Dermoscopy of a skin lesion:
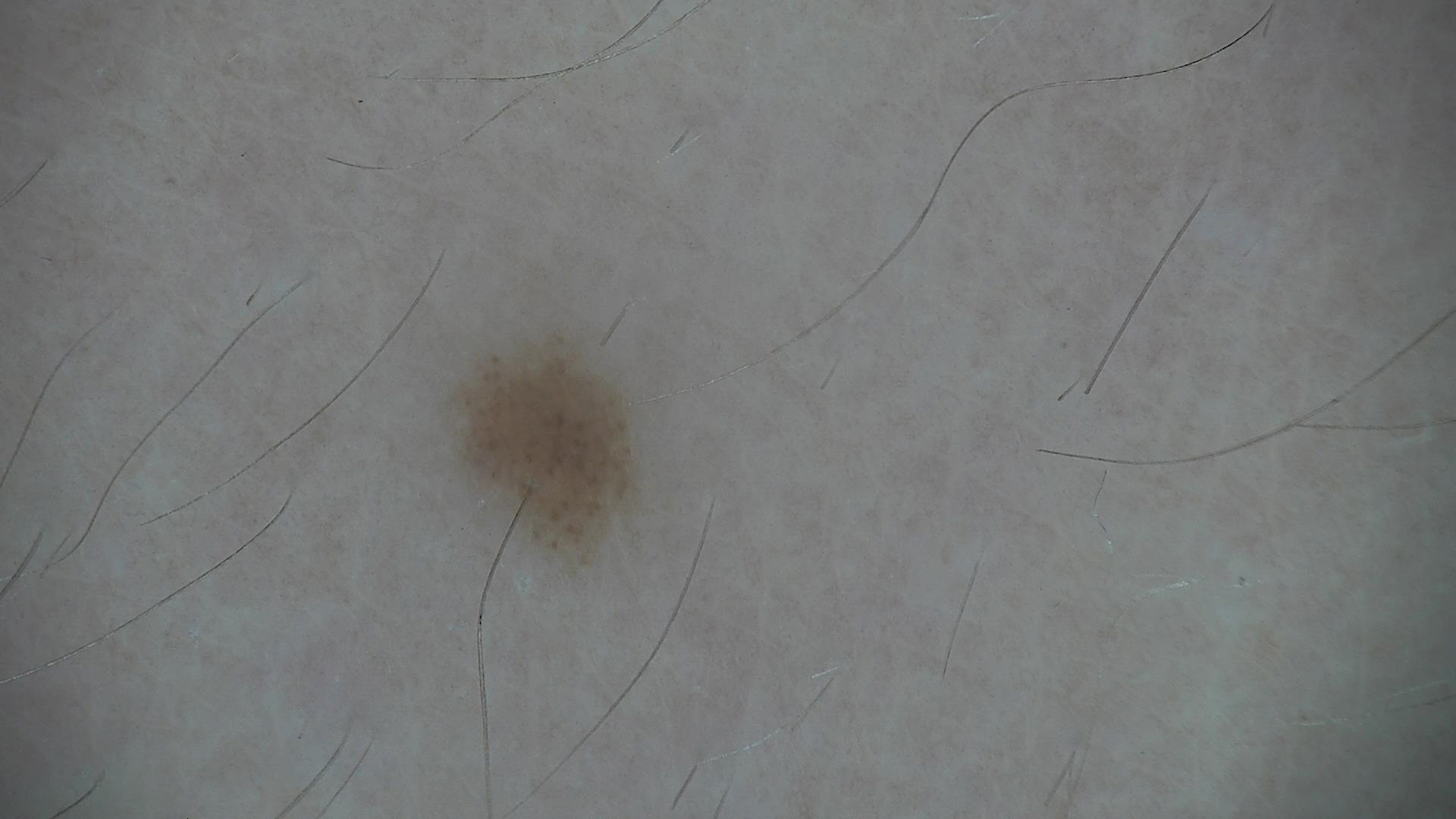<case>
<diagnosis>
<name>dysplastic junctional nevus</name>
<code>jd</code>
<malignancy>benign</malignancy>
<super_class>melanocytic</super_class>
<confirmation>expert consensus</confirmation>
</diagnosis>
</case>